This is a close-up image · located on the leg: 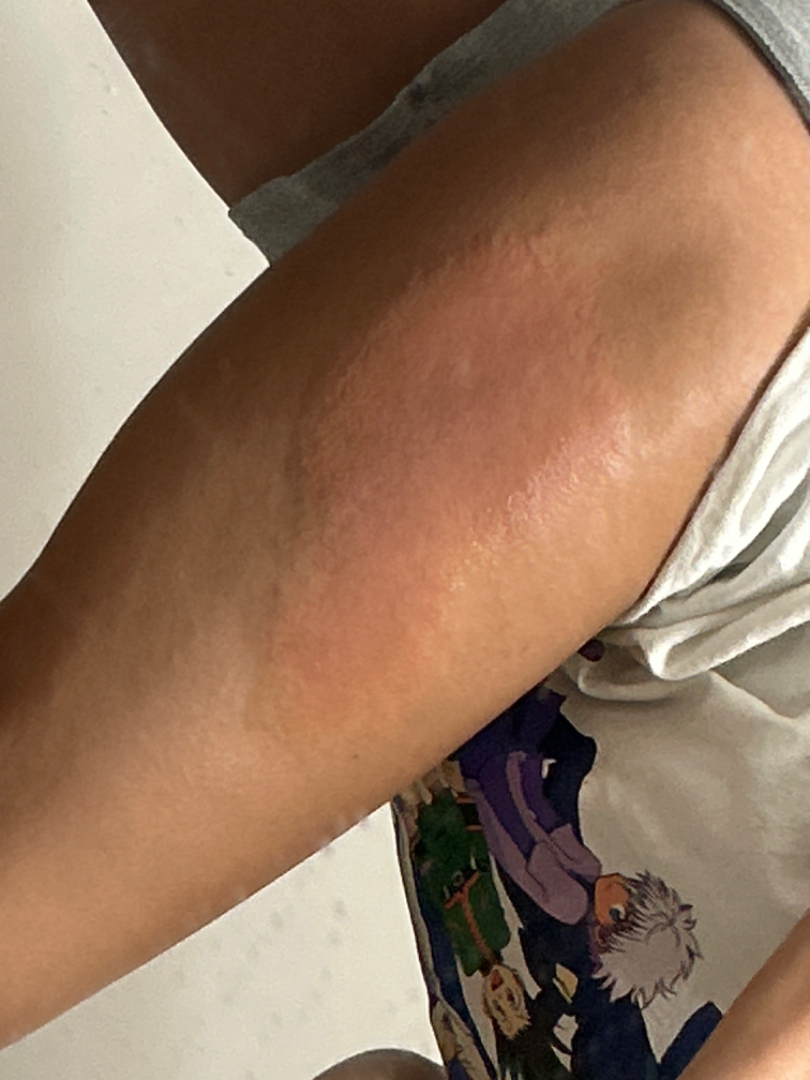Q: Duration?
A: less than one week
Q: Texture?
A: raised or bumpy
Q: What is the dermatologist's impression?
A: favoring Urticaria